Symptoms reported: itching · the photograph is a close-up of the affected area · texture is reported as raised or bumpy · self-categorized by the patient as a rash · the lesion involves the head or neck · the contributor notes the condition has been present for about one day — 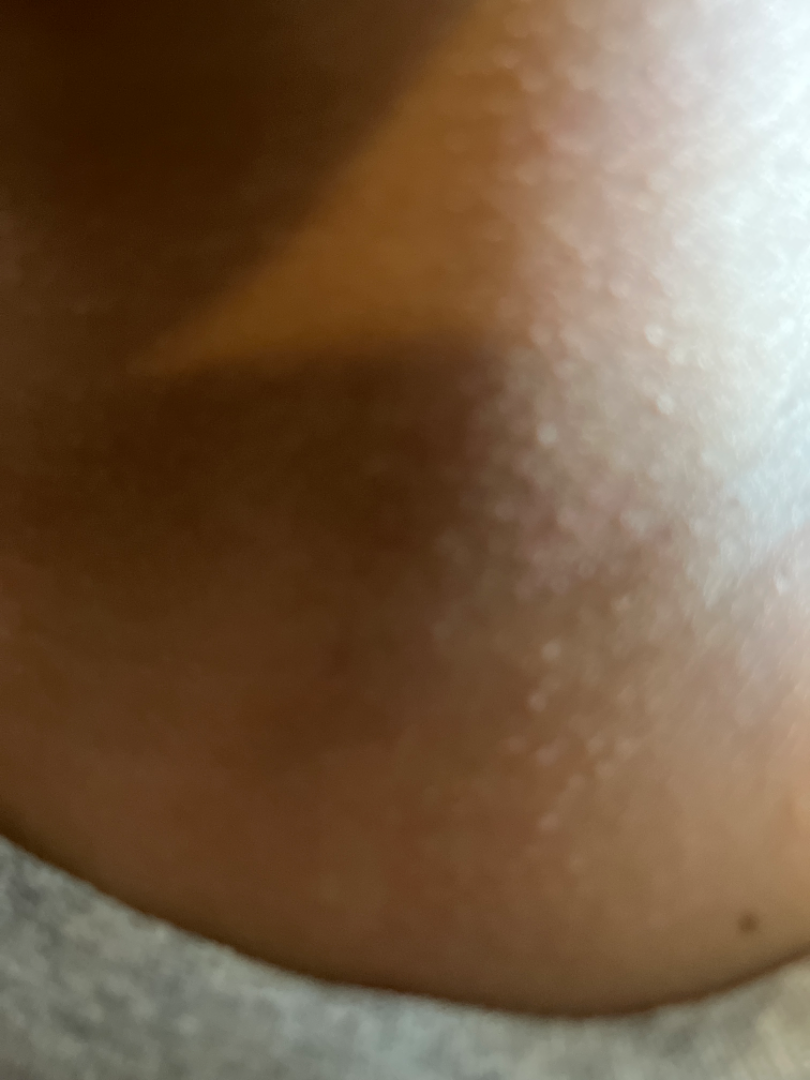assessment: indeterminate